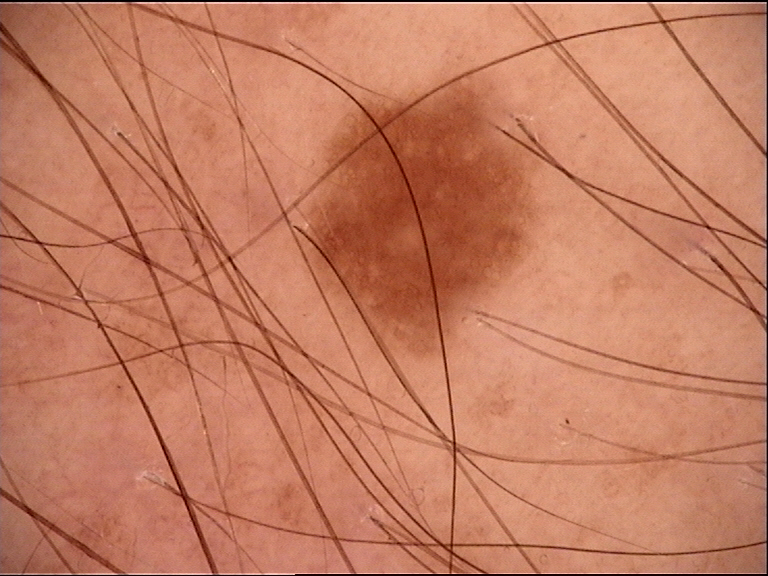A dermoscopy image of a single skin lesion. The diagnostic label was a benign lesion — a dysplastic junctional nevus.